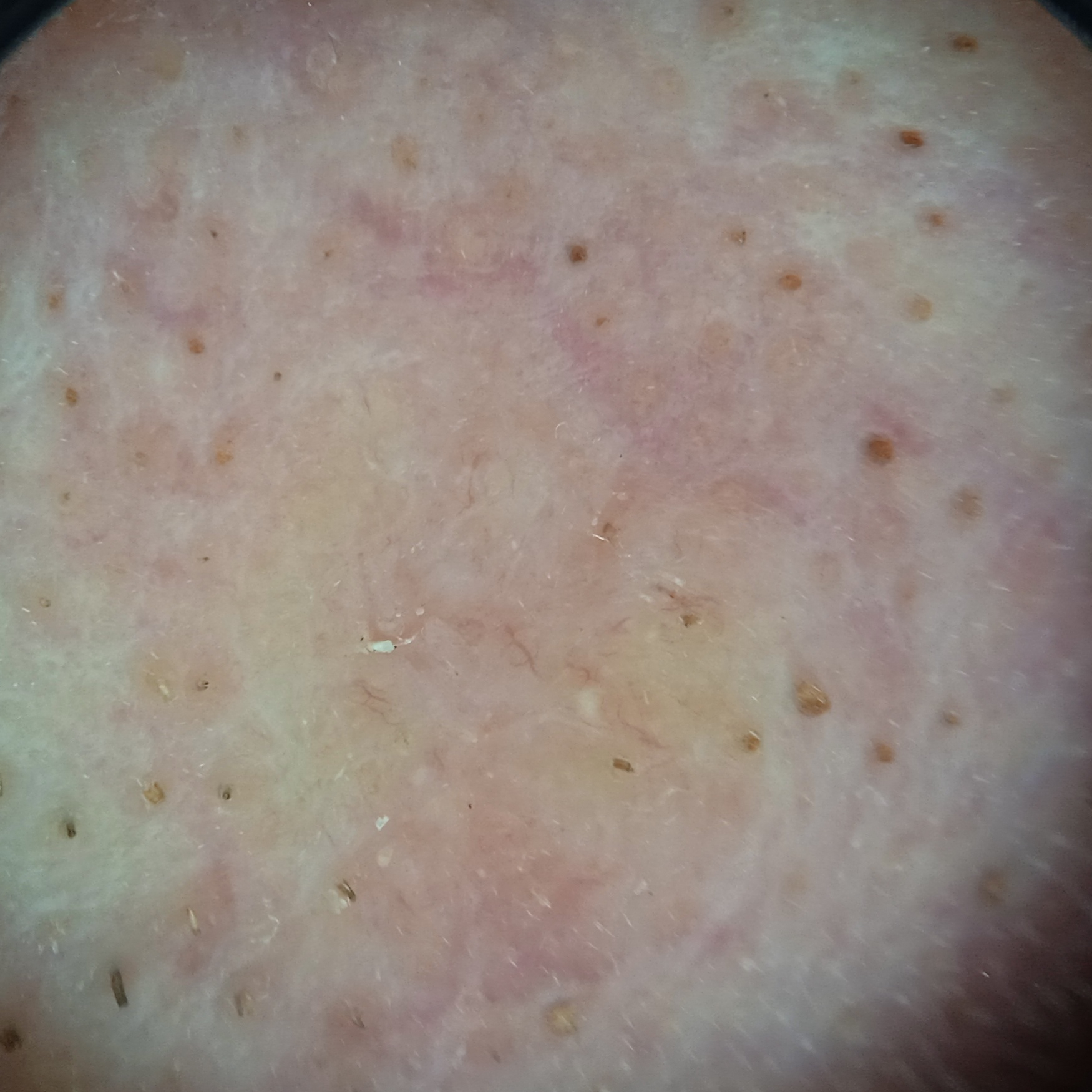risk factors = no family history of skin cancer | sun reaction = skin reddens with sun exposure | lesion size = 8.5 mm | diagnostic label = basal cell carcinoma (biopsy-proven).